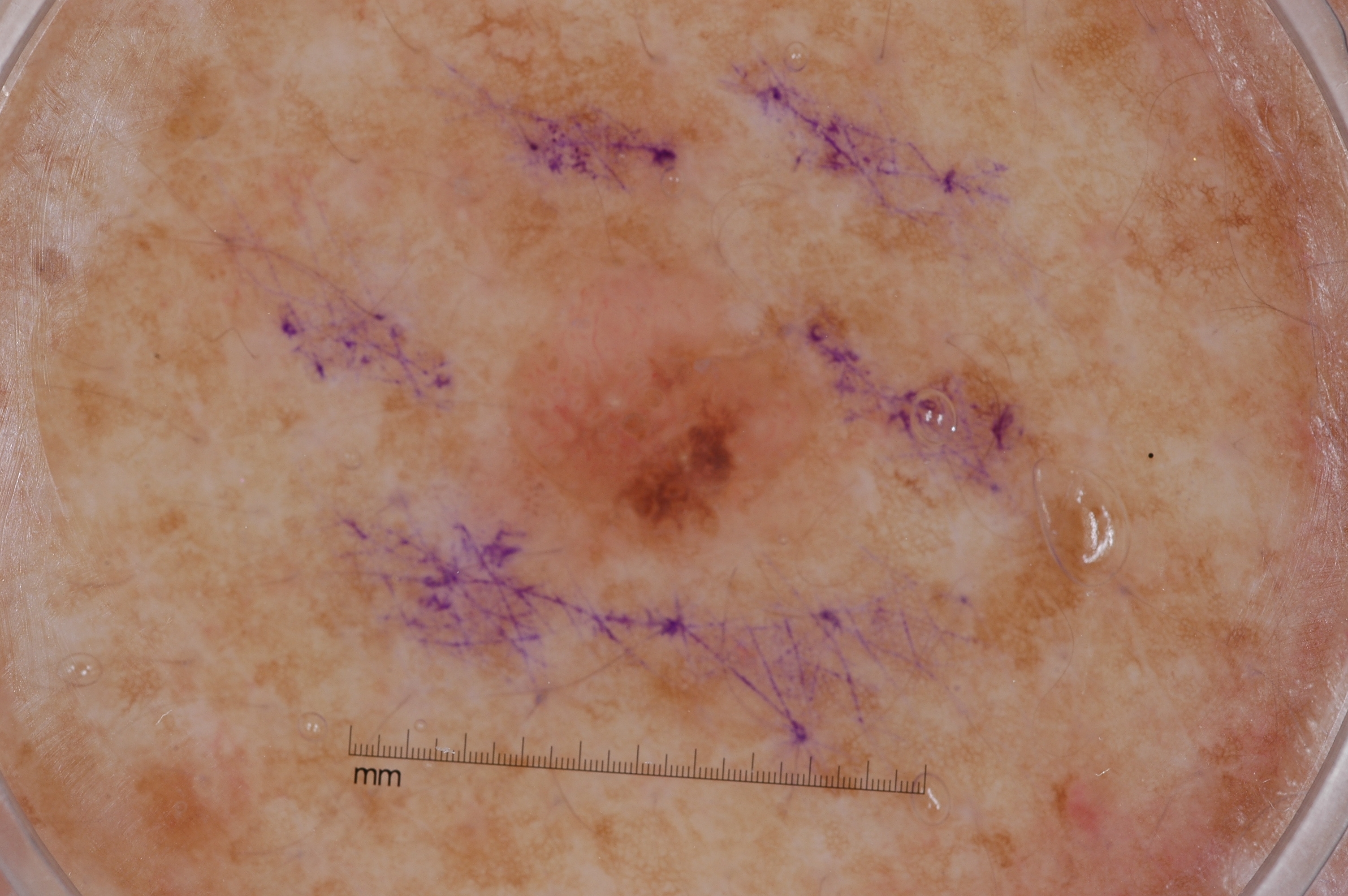{"image": {"modality": "dermoscopy"}, "patient": {"sex": "female", "age_approx": 40}, "lesion_location": {"bbox_xyxy": [503, 254, 819, 555]}, "dermoscopic_features": {"present": ["milia-like cysts"], "absent": ["negative network", "streaks", "pigment network"]}, "diagnosis": {"name": "seborrheic keratosis", "malignancy": "benign", "lineage": "keratinocytic", "provenance": "clinical"}}